This is a dermoscopic photograph of a skin lesion. A female subject, approximately 60 years of age:
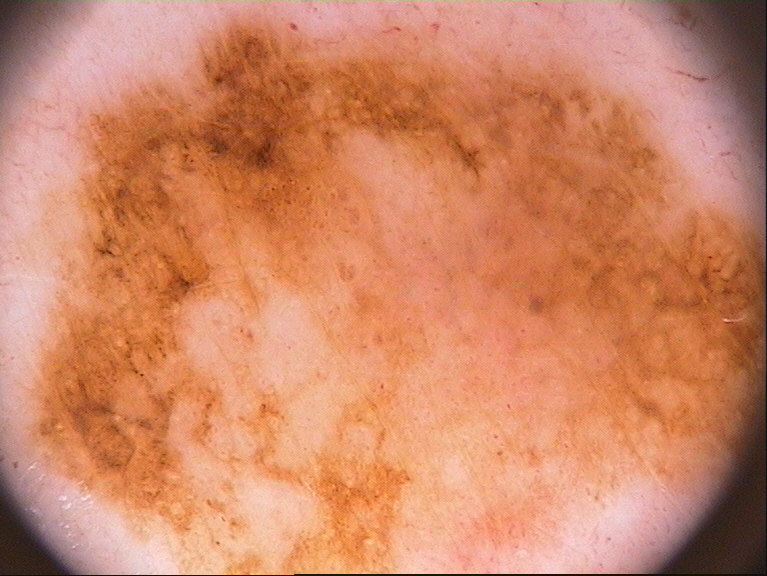* features — globules and pigment network
* lesion extent — spans the dermoscopic field
* assessment — a melanoma, a skin cancer